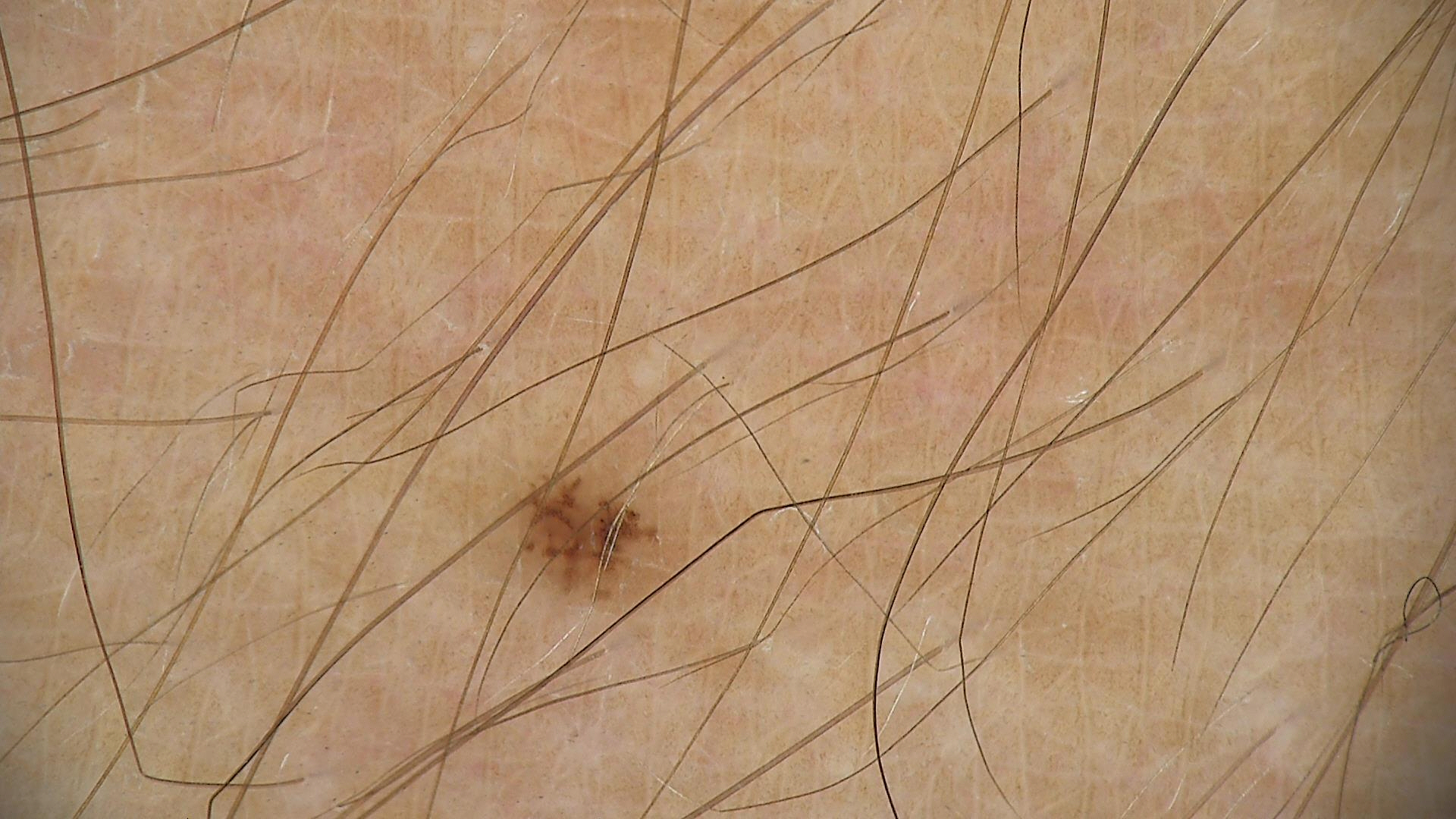class = dysplastic junctional nevus (expert consensus).